A close-up photograph; female contributor, age 30–39; the lesion involves the top or side of the foot:
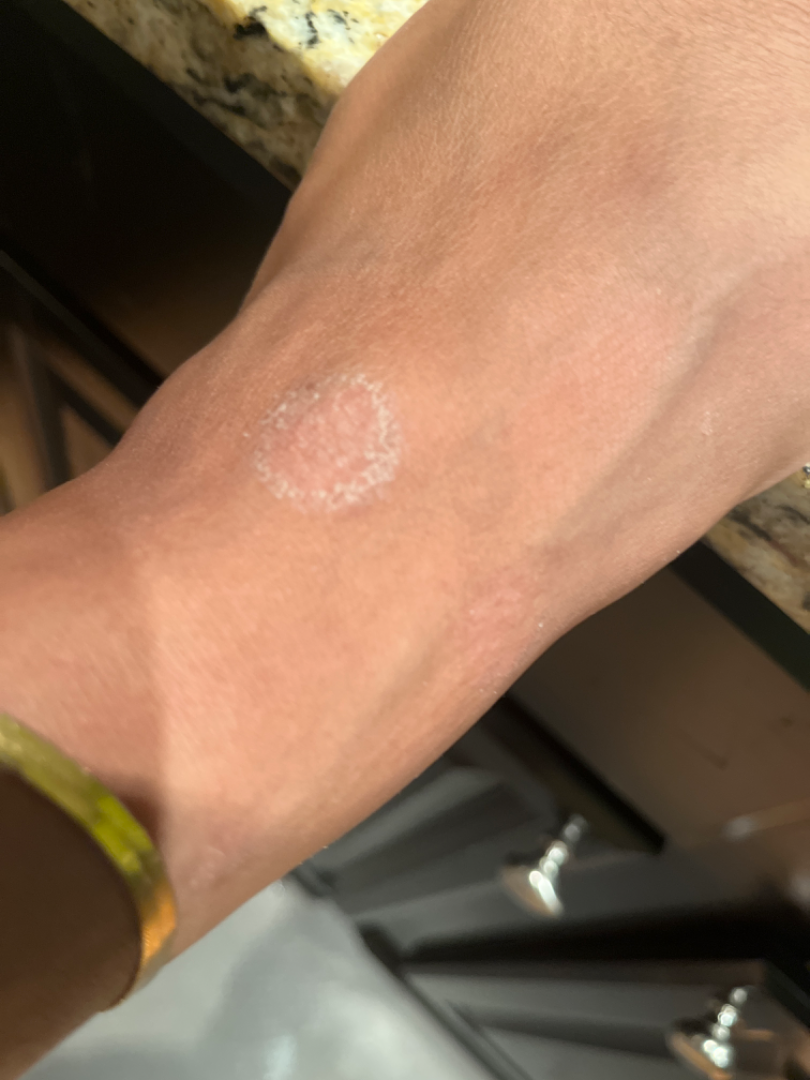Most consistent with Eczema; with consideration of Tinea.